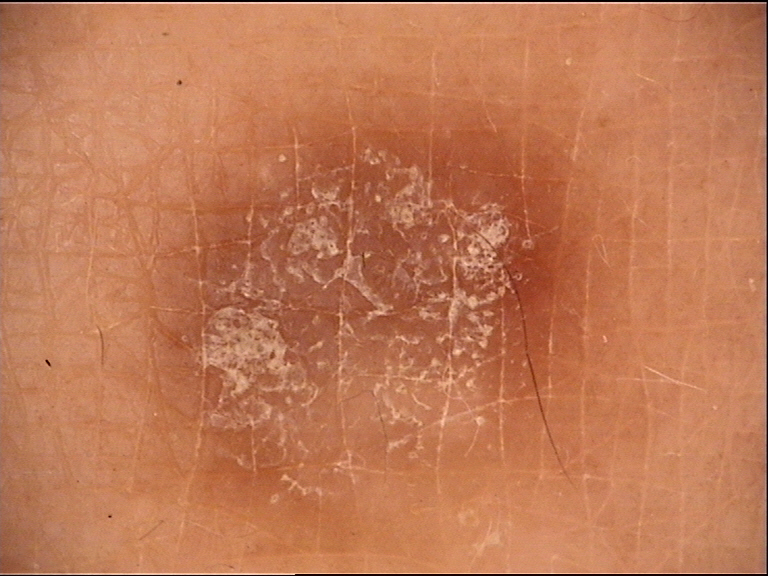A dermoscopic image of a skin lesion. The diagnosis was a fibro-histiocytic lesion — a dermatofibroma.